A male patient 72 years of age; the patient describes having a moderate number of moles; acquired for a research image collection, with no referral diagnosis; a skin lesion imaged with a dermatoscope; the patient reports no personal history of cancer and no immunosuppression; the patient says their skin tans without first burning — 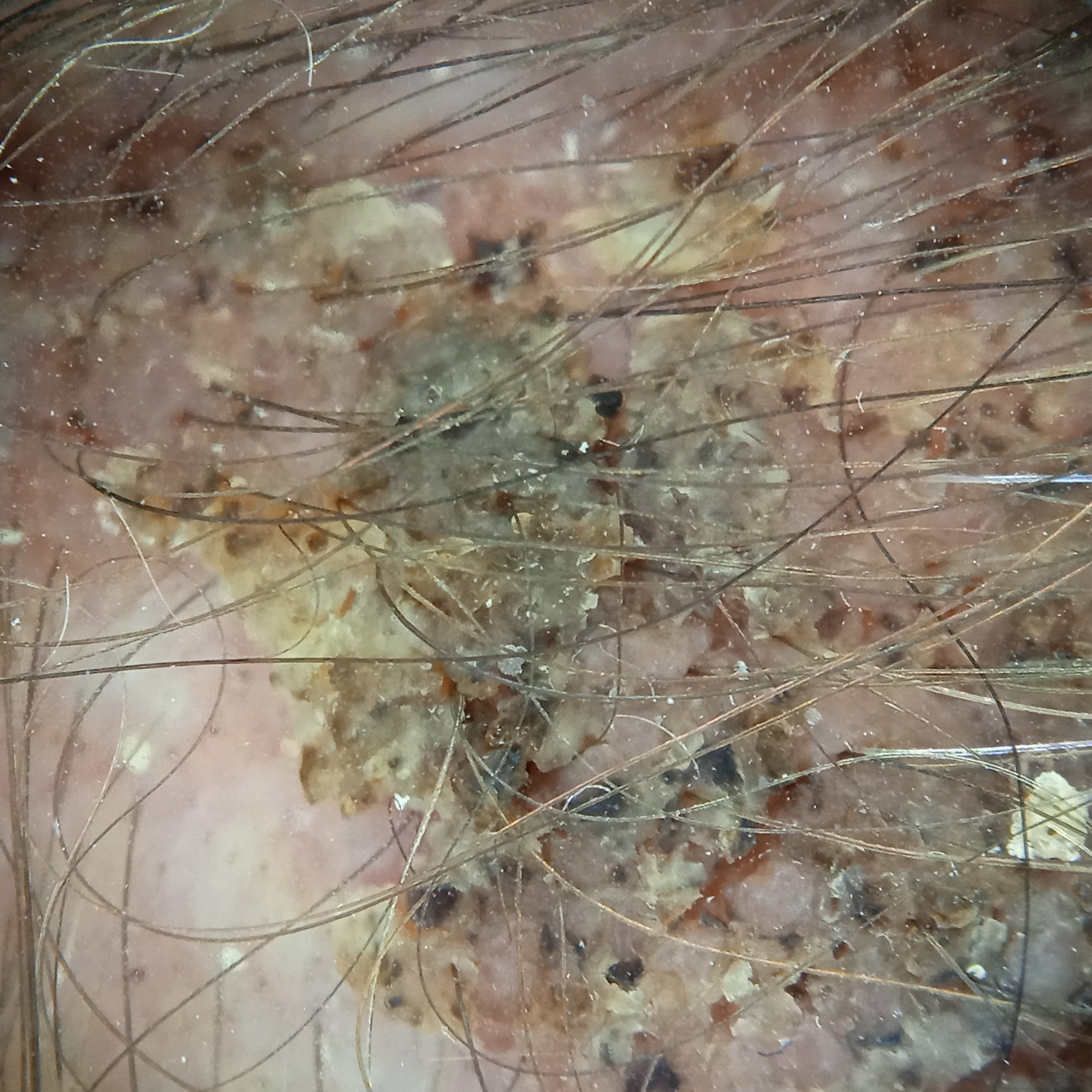Summary:
Located on the head. Measuring roughly 19.2 mm.
Conclusion:
Dermatologist review favored a seborrheic keratosis.